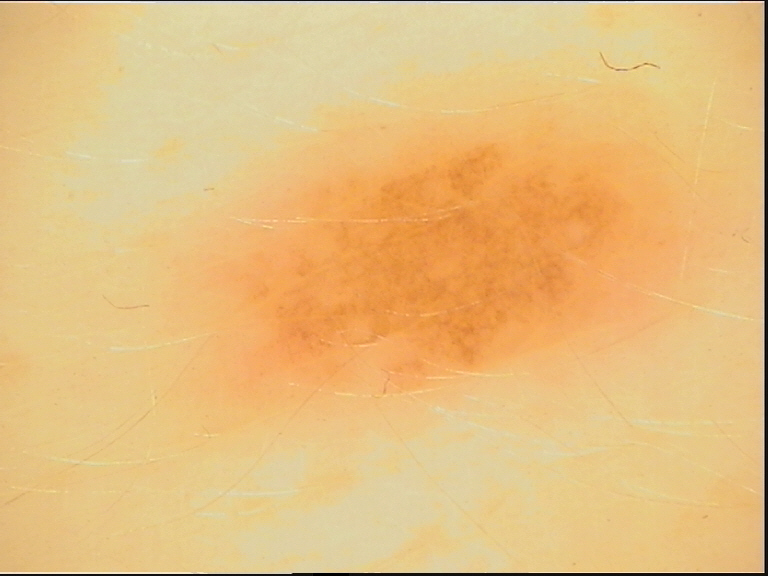Conclusion:
Diagnosed as a benign lesion — a dysplastic junctional nevus.